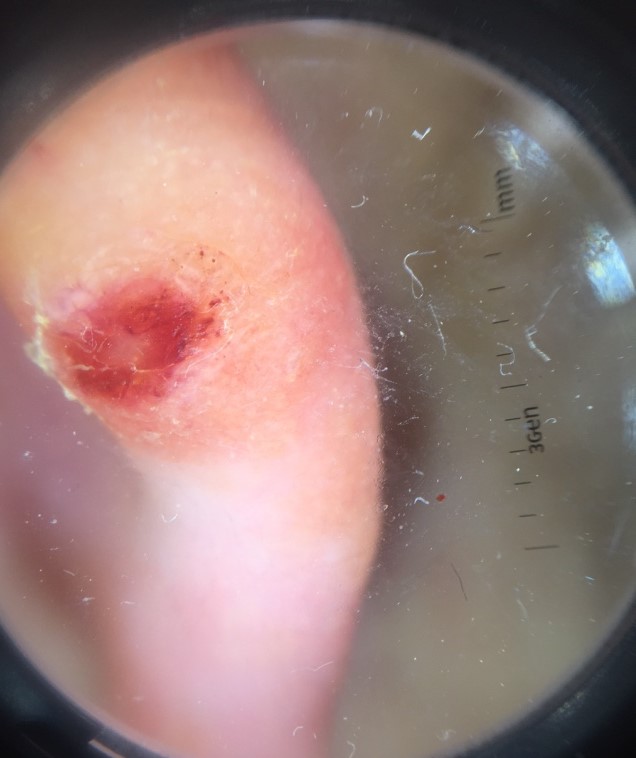Conclusion: Histopathology confirmed a squamous cell carcinoma.